A skin lesion imaged with a dermatoscope; a female subject aged 33-37; Fitzpatrick skin type III; the chart records melanoma in a first-degree relative but no prior melanoma.
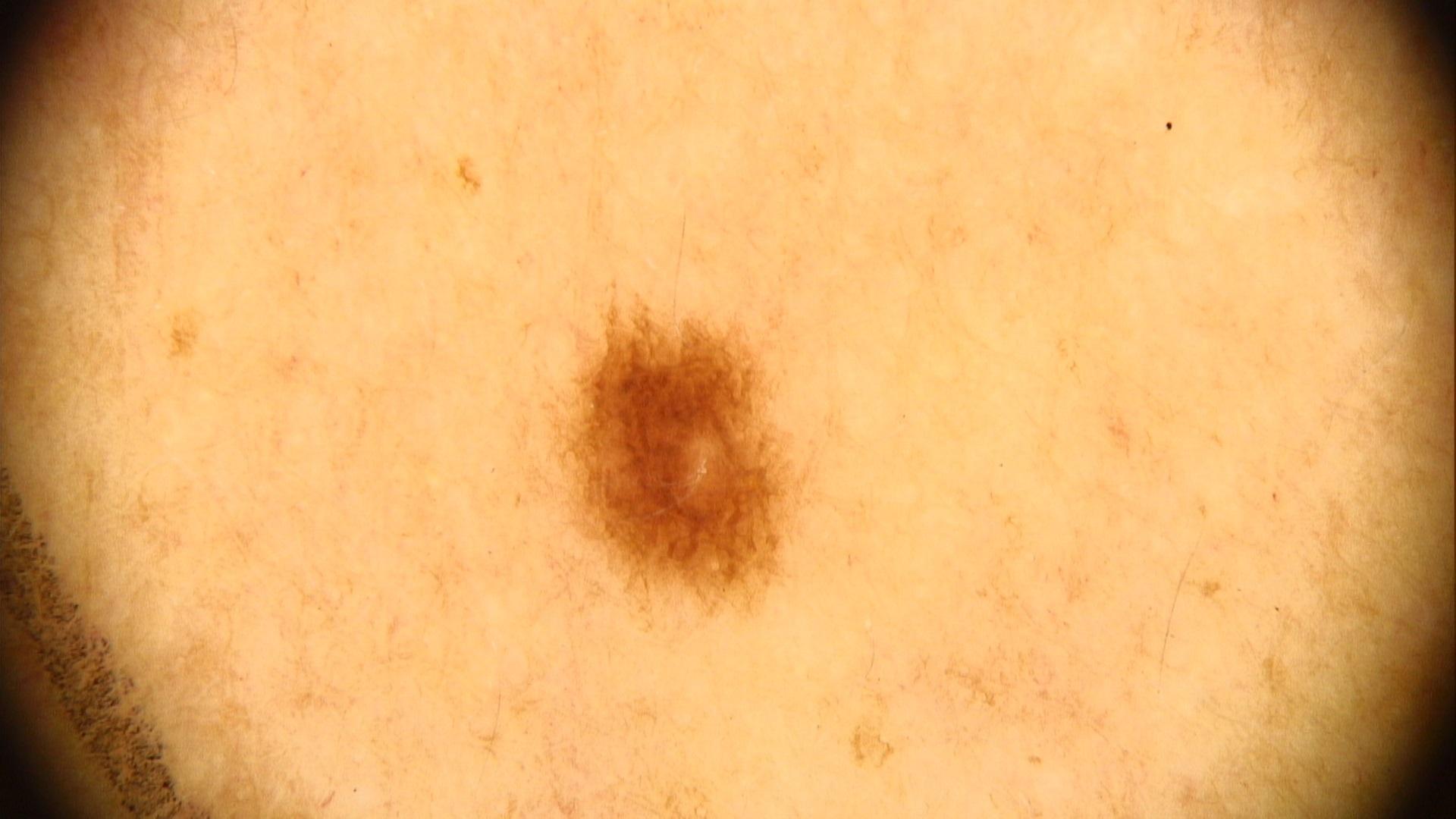Findings: The lesion involves the trunk. Conclusion: Consistent with a benign, melanocytic lesion — a nevus.